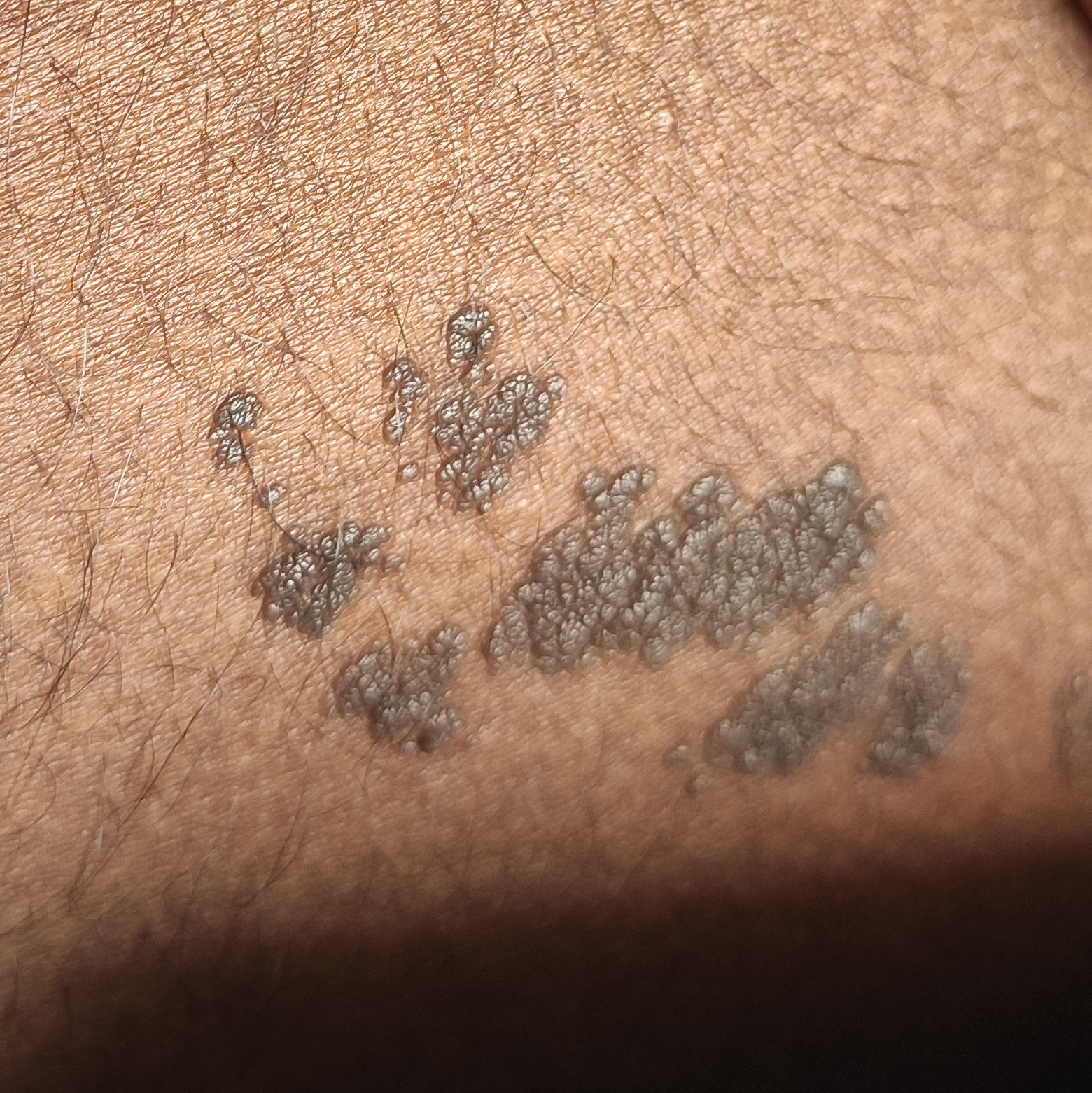diagnosis = nevus (clinical consensus).